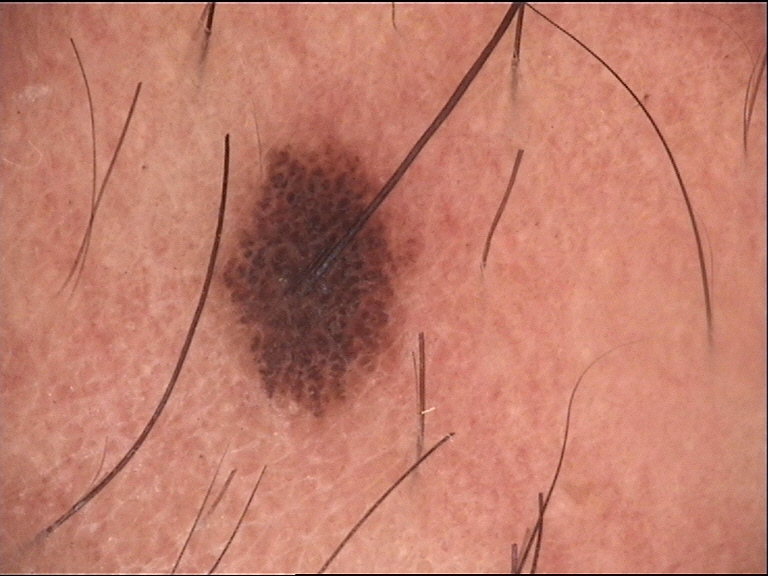A skin lesion imaged with a dermatoscope. The architecture is that of a banal lesion. Diagnosed as a compound nevus.